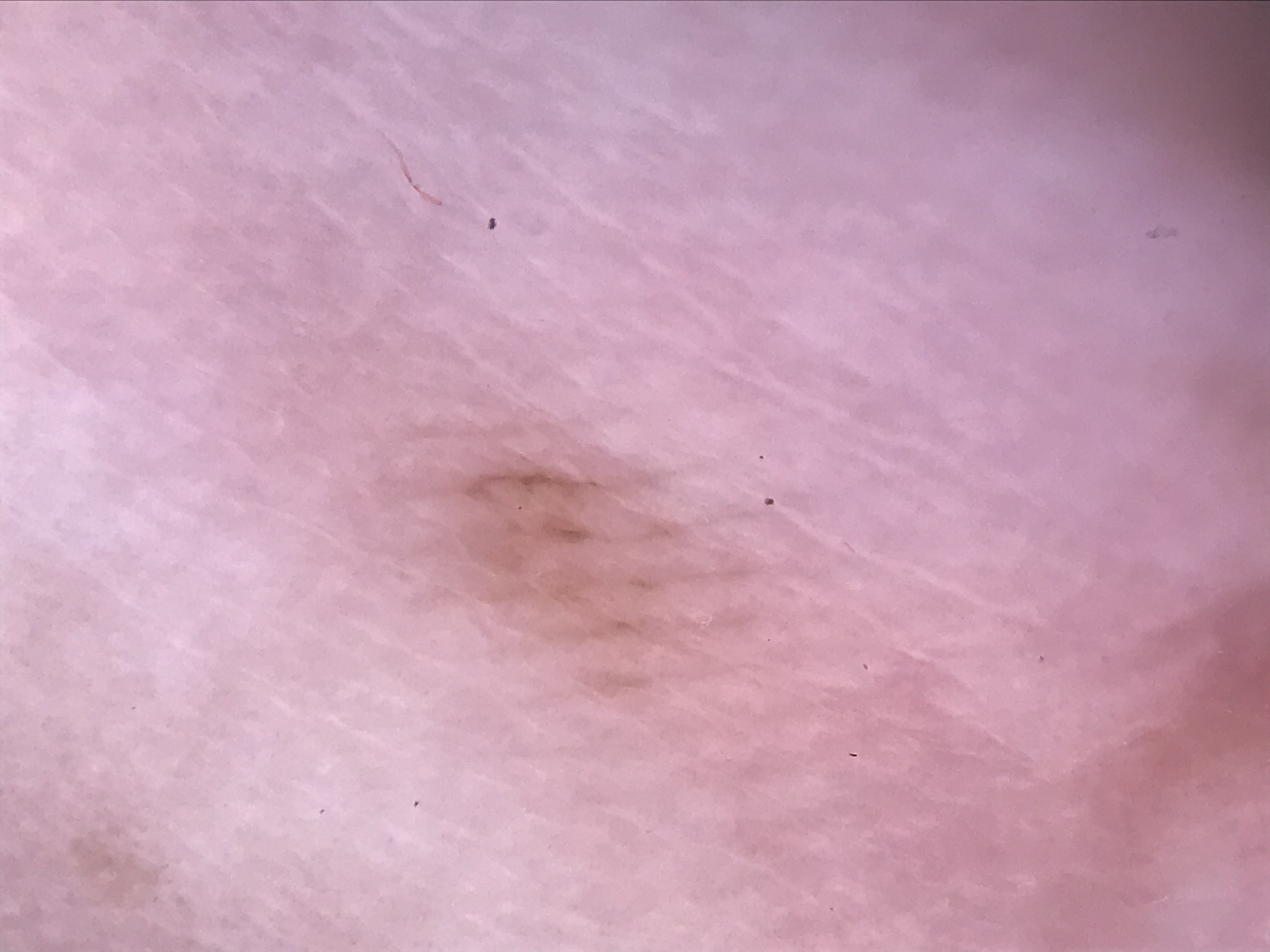A dermatoscopic image of a skin lesion.
The architecture is that of a banal lesion.
Classified as an acral junctional nevus.